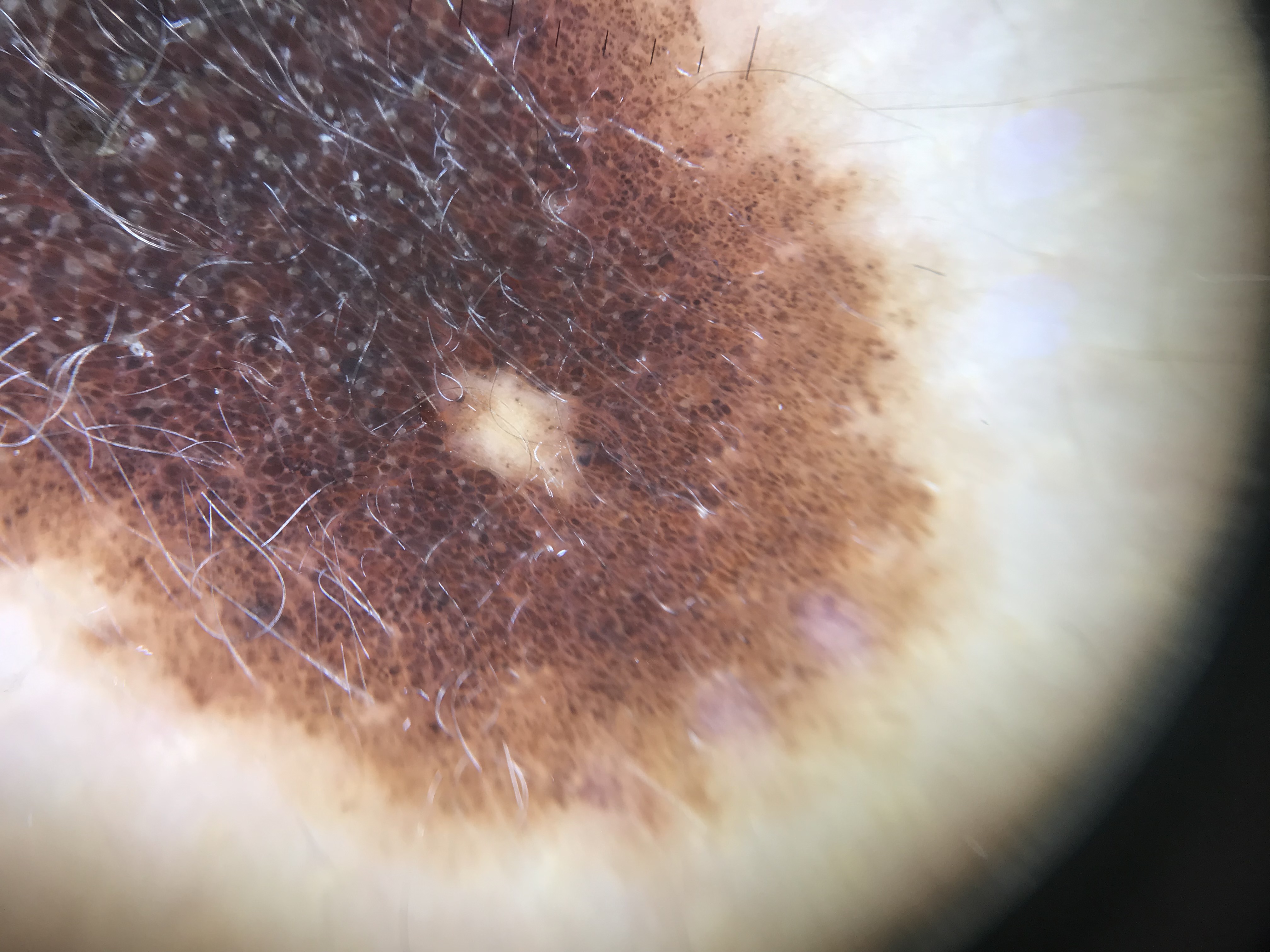– classification — banal
– diagnosis — congenital compound nevus (expert consensus)